A dermatoscopic image of a skin lesion.
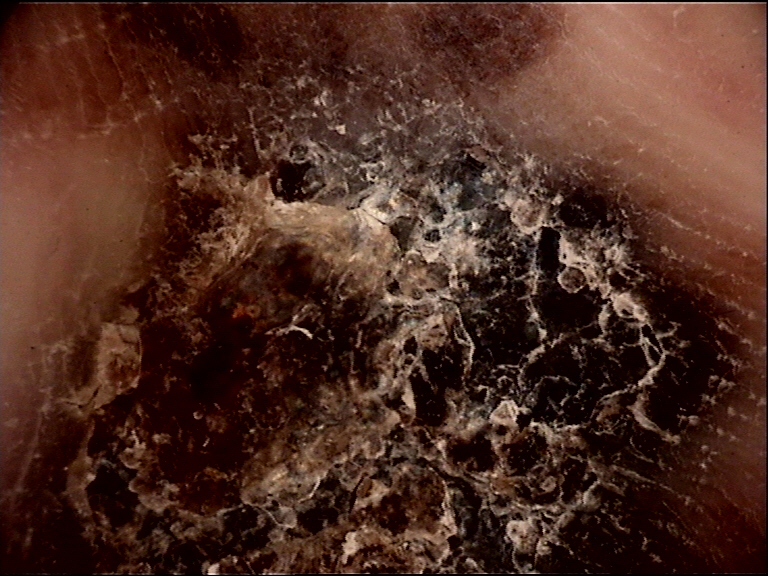<dermoscopy>
<diagnosis>
<name>acral lentiginous melanoma</name>
<code>alm</code>
<malignancy>malignant</malignancy>
<super_class>melanocytic</super_class>
<confirmation>histopathology</confirmation>
</diagnosis>
</dermoscopy>